A dermatoscopic image of a skin lesion: 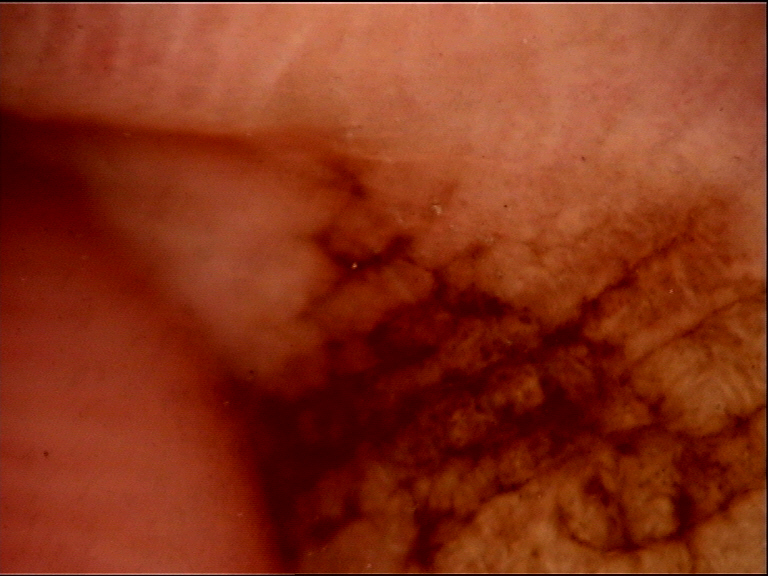Conclusion: The diagnostic label was an acral dysplastic junctional nevus.